A dermoscopic photograph of a skin lesion:
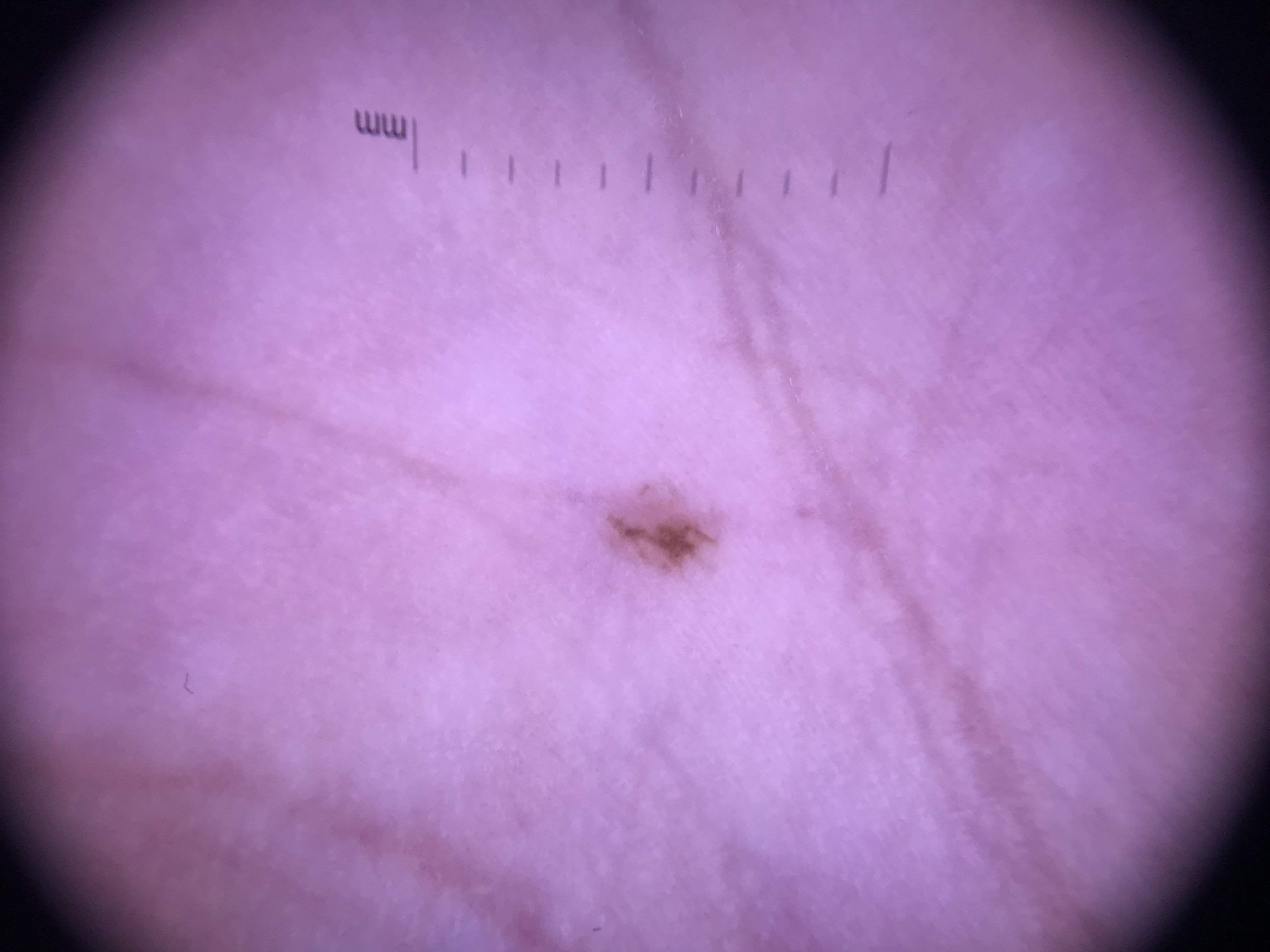class: acral dysplastic junctional nevus (expert consensus).